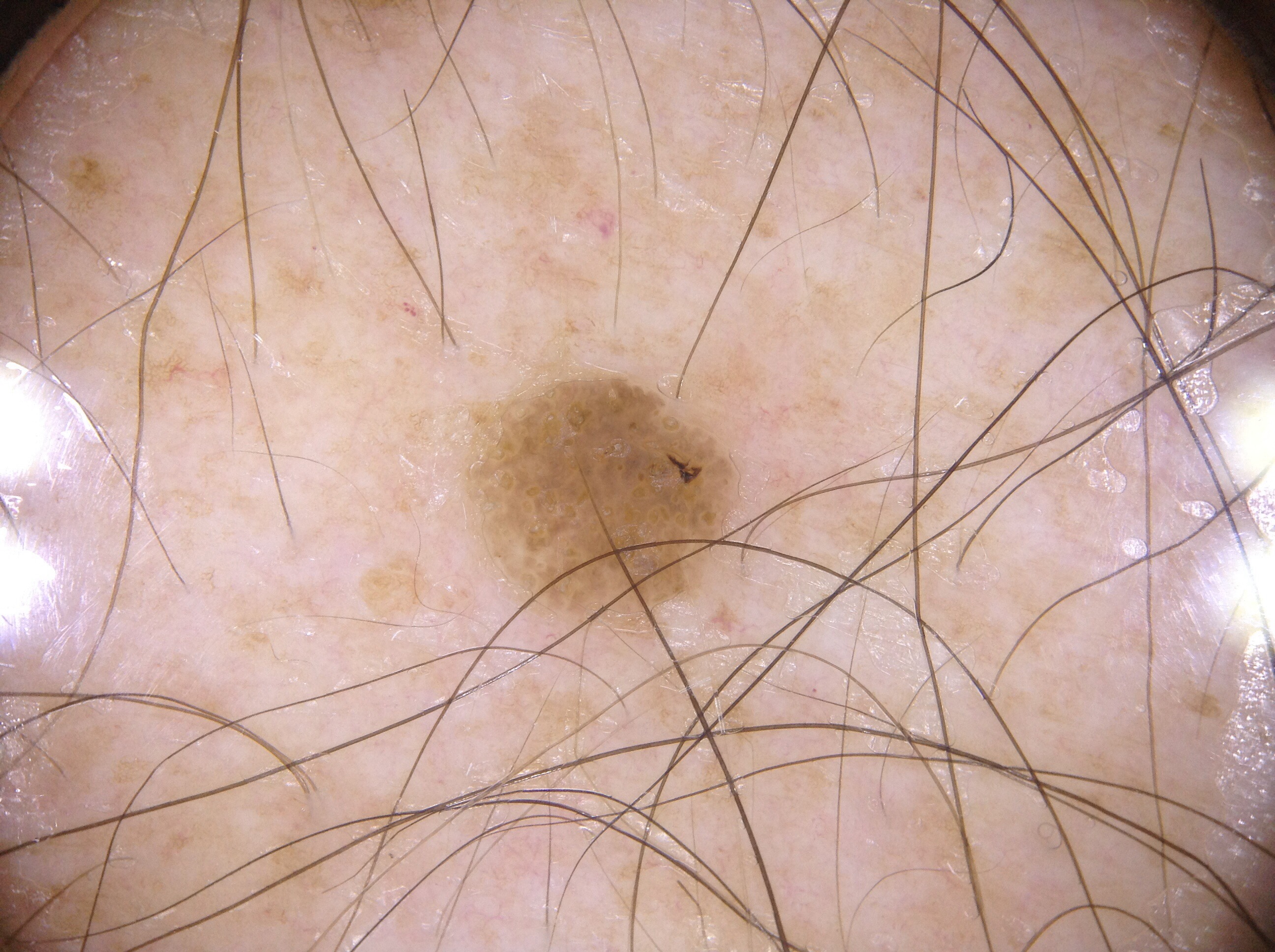  image:
    modality: dermoscopy
  dermoscopic_features:
    present: []
    absent:
      - pigment network
      - negative network
      - streaks
      - milia-like cysts
  lesion_extent:
    approx_field_fraction_pct: 4
  lesion_location:
    bbox_xyxy:
      - 488
      - 380
      - 727
      - 610
  diagnosis:
    name: seborrheic keratosis
    malignancy: benign
    lineage: keratinocytic
    provenance: clinical